The patient is a female approximately 60 years of age; a dermoscopic view of a skin lesion:
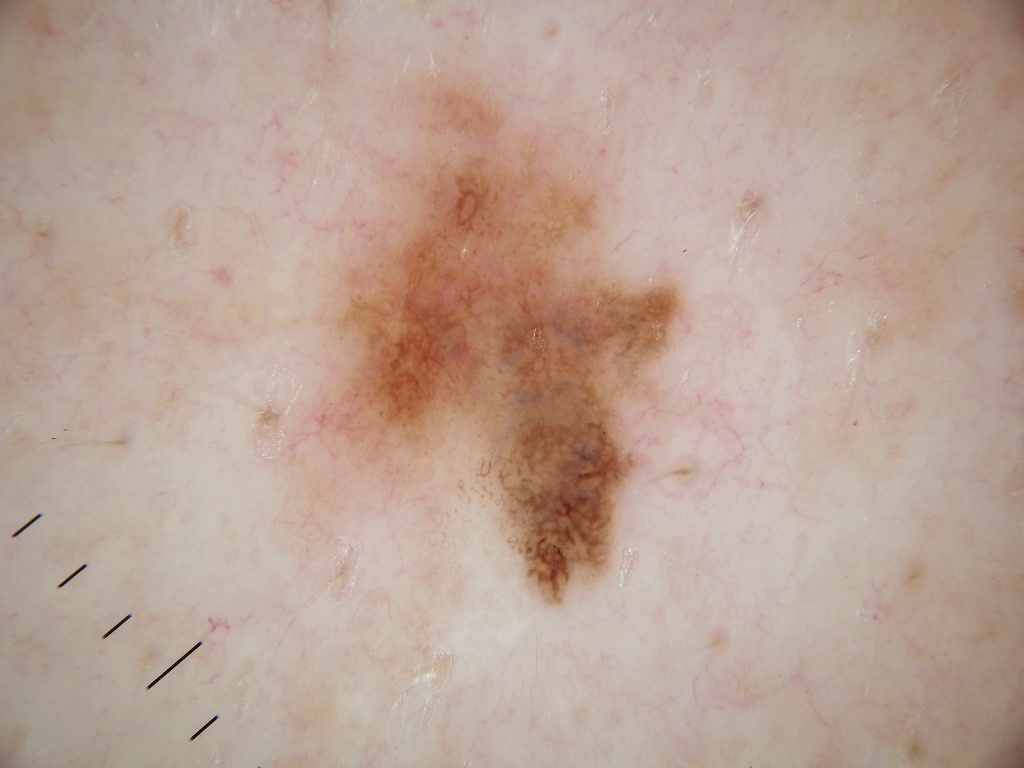The lesion occupies roughly 13% of the field.
On dermoscopy, the lesion shows pigment network, with no streaks, globules, milia-like cysts, or negative network.
The lesion occupies the region box(312, 73, 682, 602).
The clinical diagnosis was a melanocytic nevus.